Close-up view: 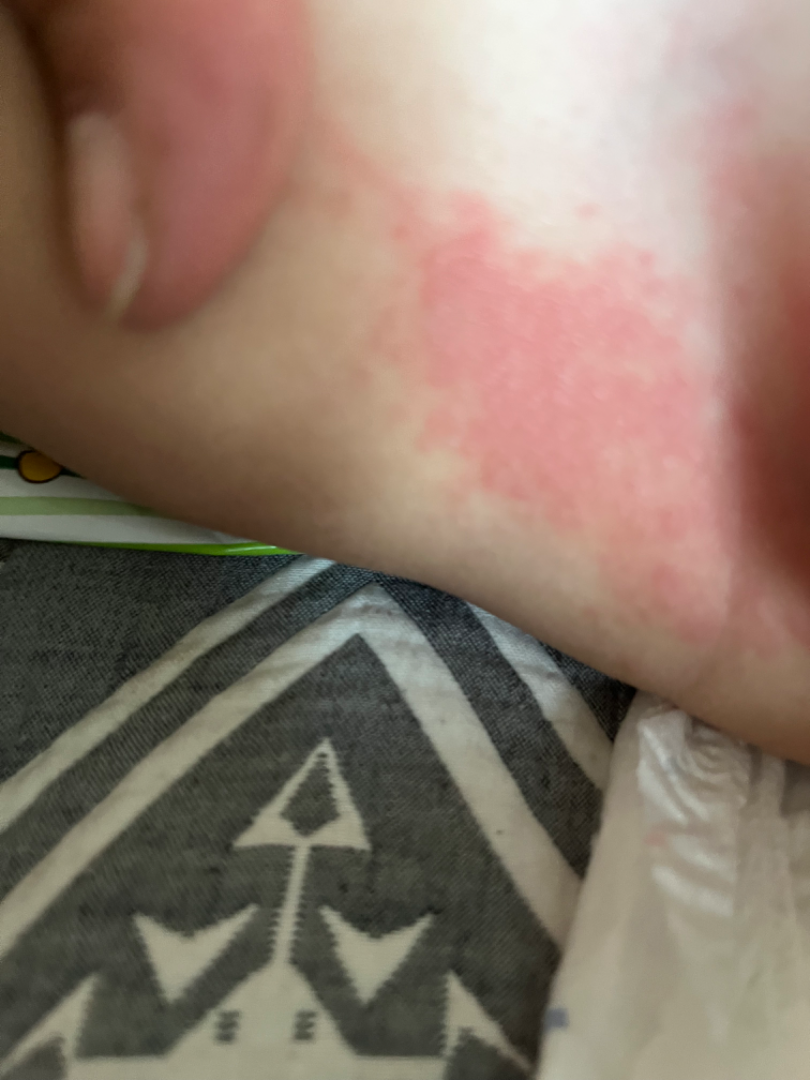The case was difficult to assess from the available photograph.